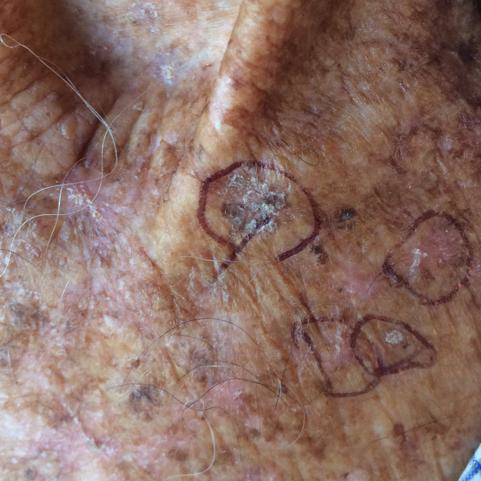History notes prior malignancy (patient or family) and pesticide exposure. A male patient 65 years of age. Recorded as FST II. Located on the chest. The lesion measures approximately 35 × 15 mm. The patient describes that the lesion has bled and itches, but does not hurt. Clinically diagnosed as an actinic keratosis.